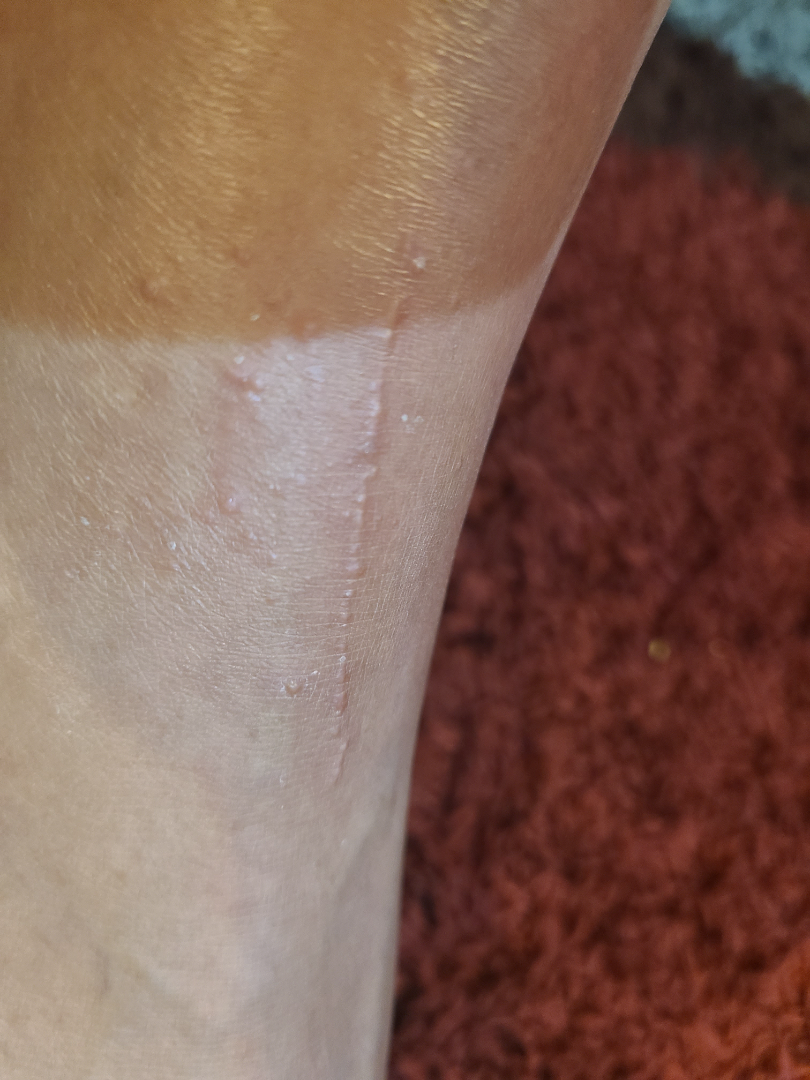The photograph was taken at an angle.
Symptoms reported: itching.
Present for one to four weeks.
The patient is 40–49, male.
The lesion involves the leg.
On teledermatology review: the differential, in no particular order, includes Lichen planus/lichenoid eruption, Koebner phenomenon and Allergic Contact Dermatitis; less likely is Lichen nitidus; less probable is Verruca vulgaris.